A dermatoscopic image of a skin lesion.
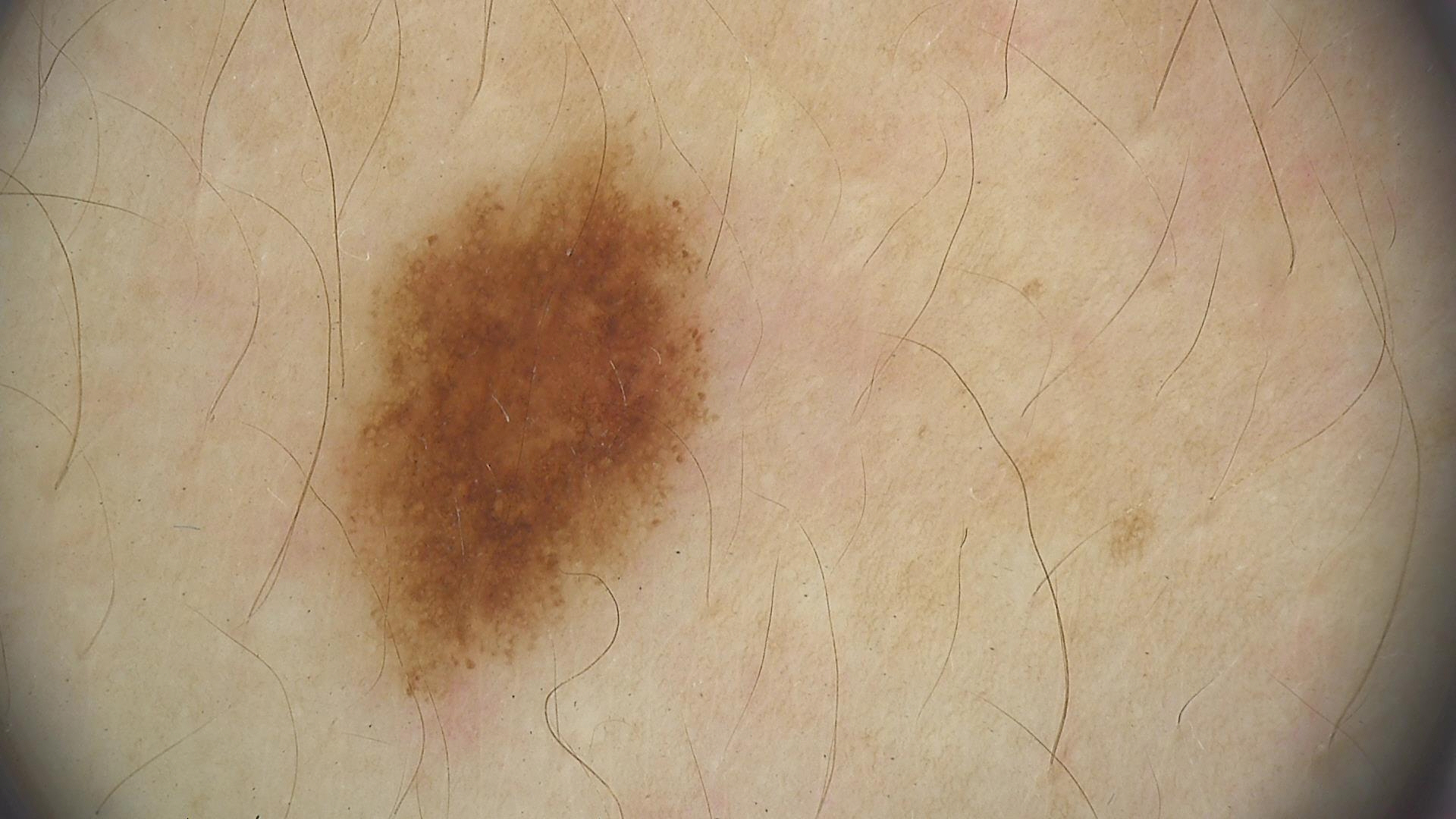Impression: The diagnosis was a benign lesion — a dysplastic junctional nevus.